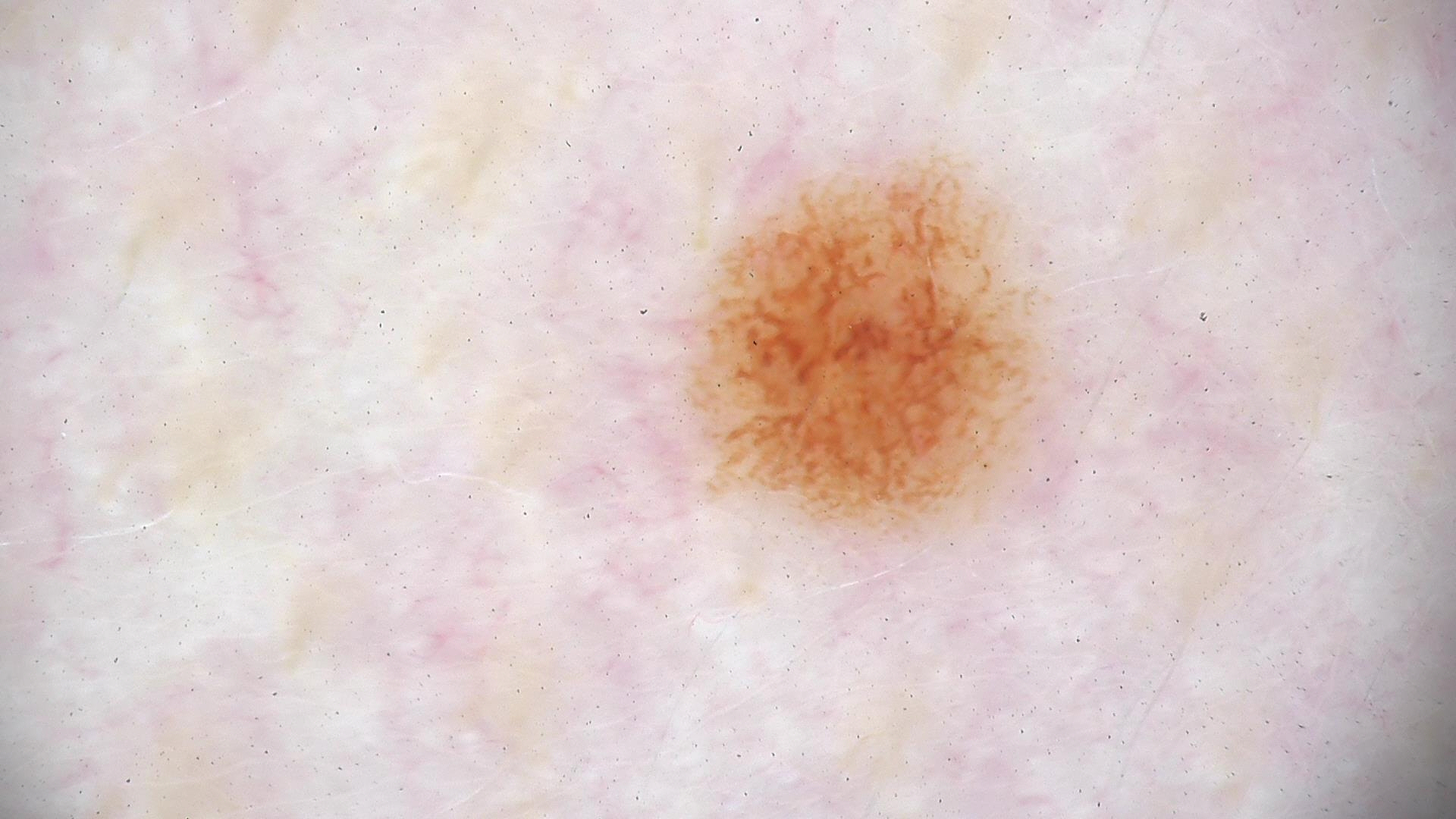{
  "image": "dermatoscopy",
  "diagnosis": {
    "name": "dysplastic junctional nevus",
    "code": "jd",
    "malignancy": "benign",
    "super_class": "melanocytic",
    "confirmation": "expert consensus"
  }
}